The affected area is the back of the hand, leg and top or side of the foot · the patient is a male aged 50–59 · the photo was captured at an angle — 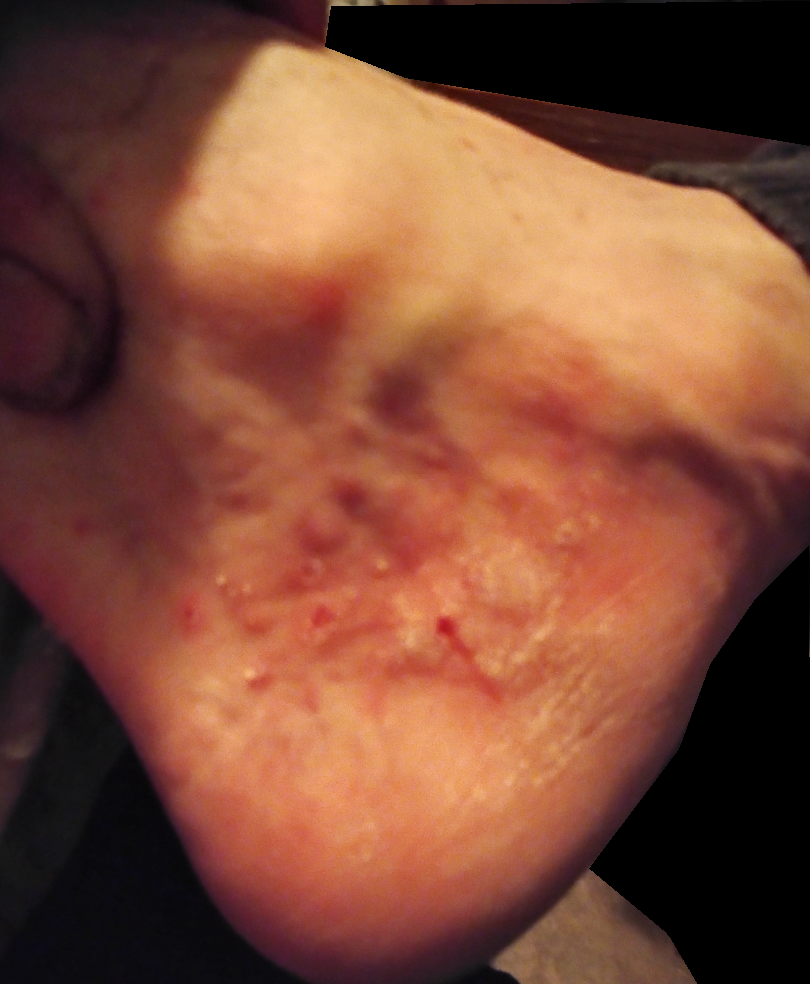Q: Could the case be diagnosed?
A: could not be assessed
Q: Reported symptoms?
A: bleeding, enlargement, burning, pain and itching
Q: When did this start?
A: more than one year
Q: Texture?
A: raised or bumpy, rough or flaky and fluid-filled
Q: Patient's own categorization?
A: a rash